Referred for assessment of suspected basal cell carcinoma. A dermoscopy image of a skin lesion. A female subject age 60.
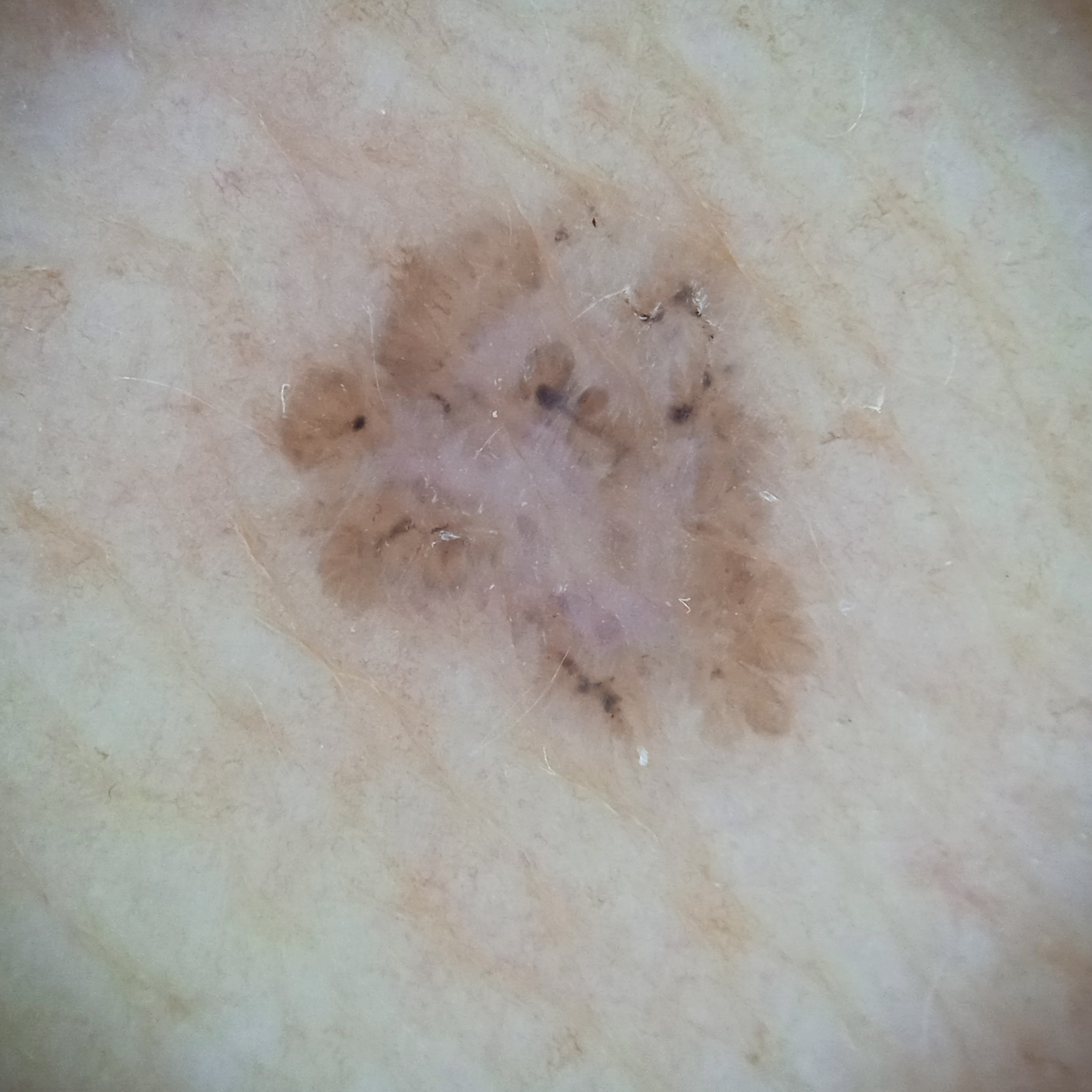| feature | finding |
|---|---|
| site | the torso |
| diagnostic label | basal cell carcinoma (dermatologist consensus) |